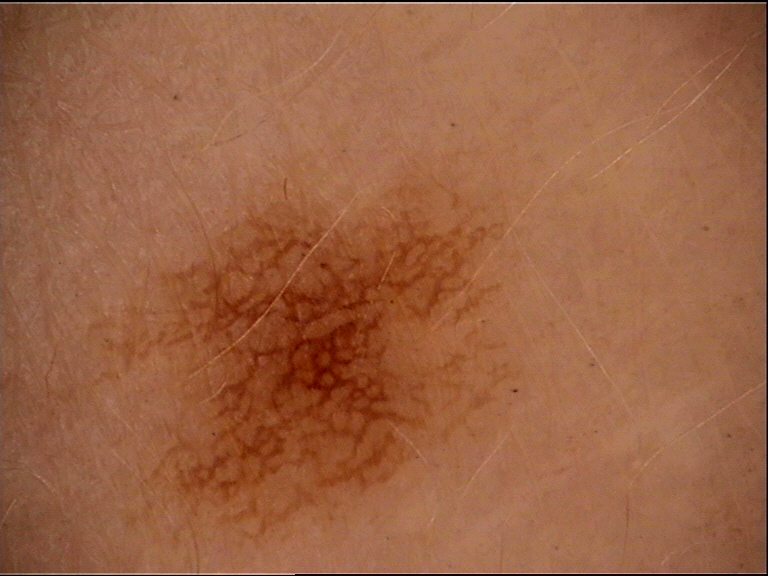A dermoscopic close-up of a skin lesion. Diagnosed as a dysplastic junctional nevus.